The patient is Fitzpatrick II; a male subject approximately 55 years of age — 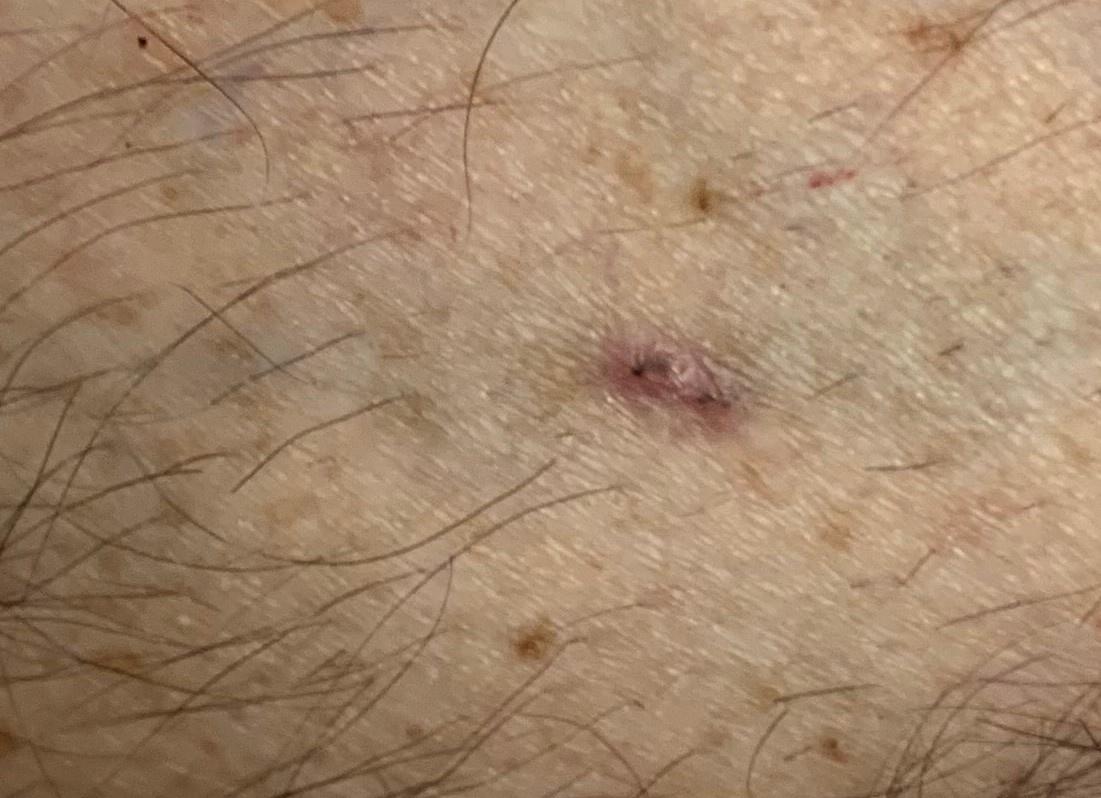Findings:
• site: a lower extremity
• diagnostic label: Basal cell carcinoma (biopsy-proven)